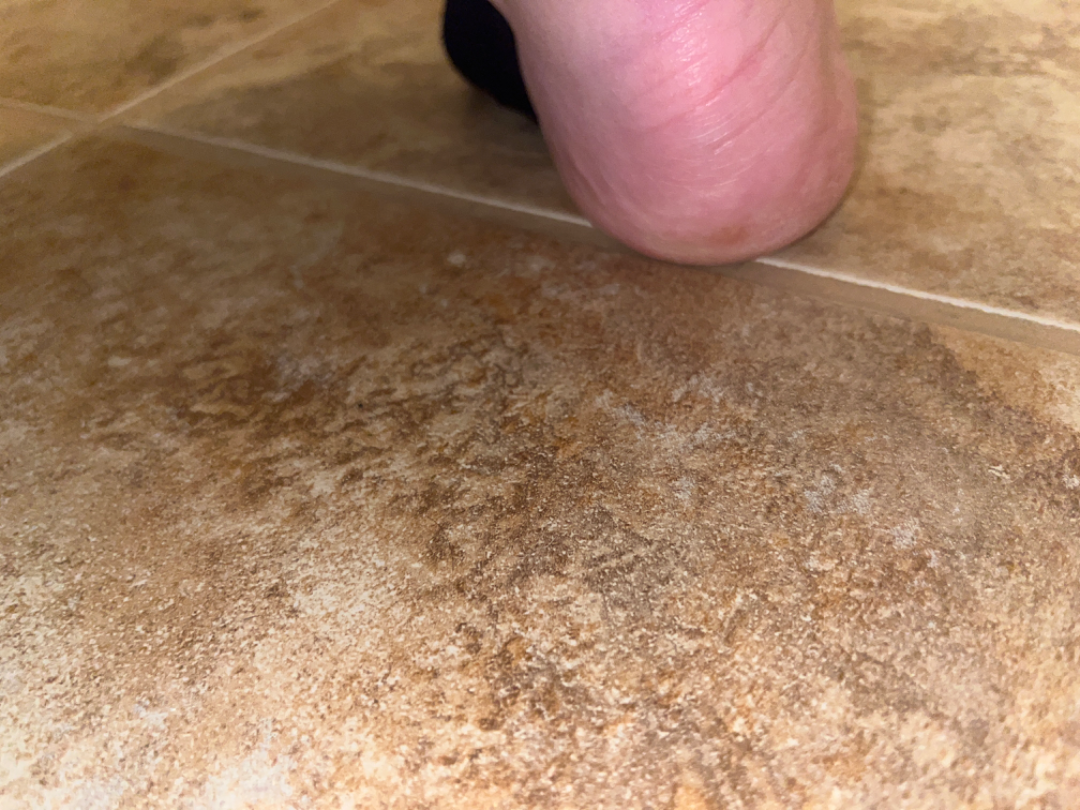The image was not sufficient for the reviewer to characterize the skin condition. Female patient, age 30–39. The lesion is associated with pain. FST II; human graders estimated Monk skin tone scale 1–2. An image taken at a distance. The lesion is described as rough or flaky and fluid-filled. Present for one to four weeks.